Located on the leg. The patient indicates associated joint pain. Symptoms reported: enlargement, itching and pain. A close-up photograph. The patient indicates the lesion is raised or bumpy. The patient considered this a rash. The subject is a female aged 40–49:
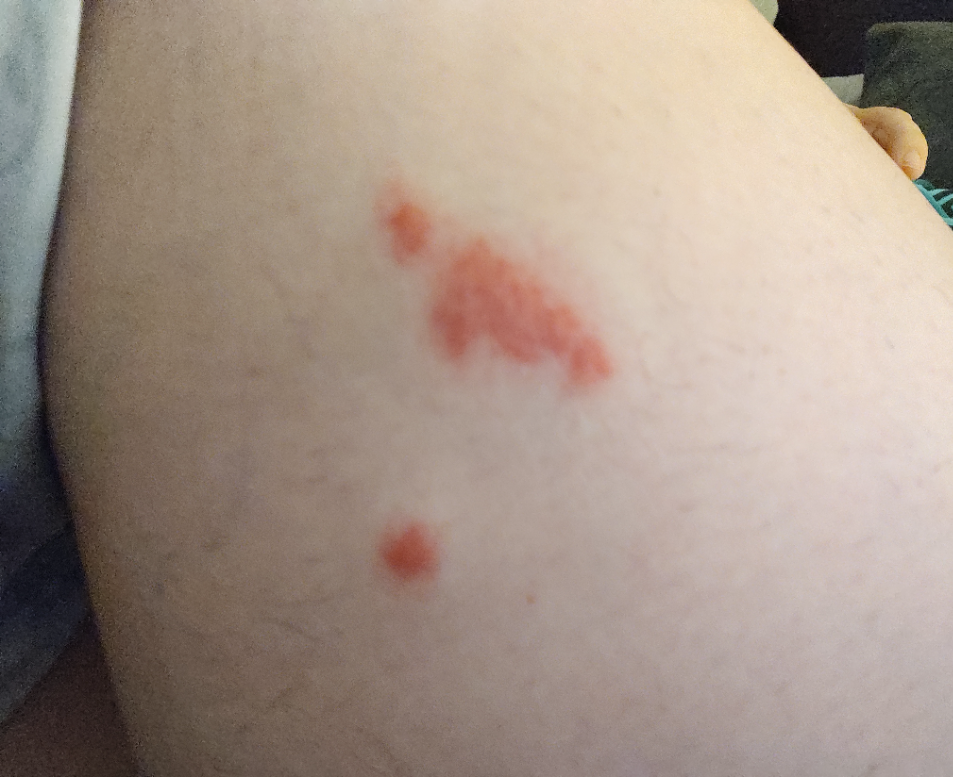The reviewing dermatologist was unable to assign a differential diagnosis from the image.